Dermoscopy of a skin lesion. The patient is a male in their mid-20s:
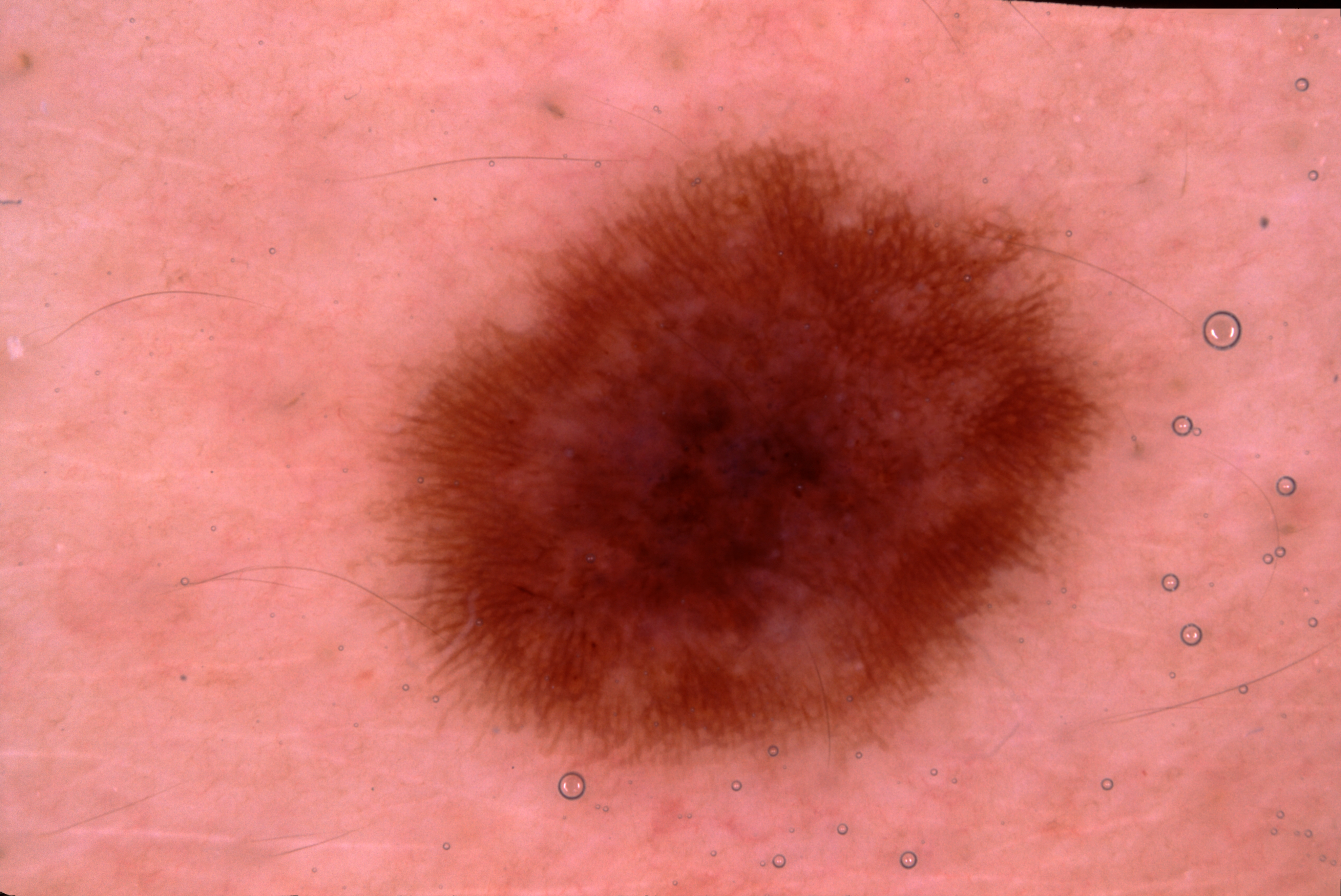Case summary:
As (left, top, right, bottom), the visible lesion spans bbox=[370, 133, 1128, 782]. The dermoscopic pattern shows pigment network.
Conclusion:
Clinically diagnosed as a melanocytic nevus.